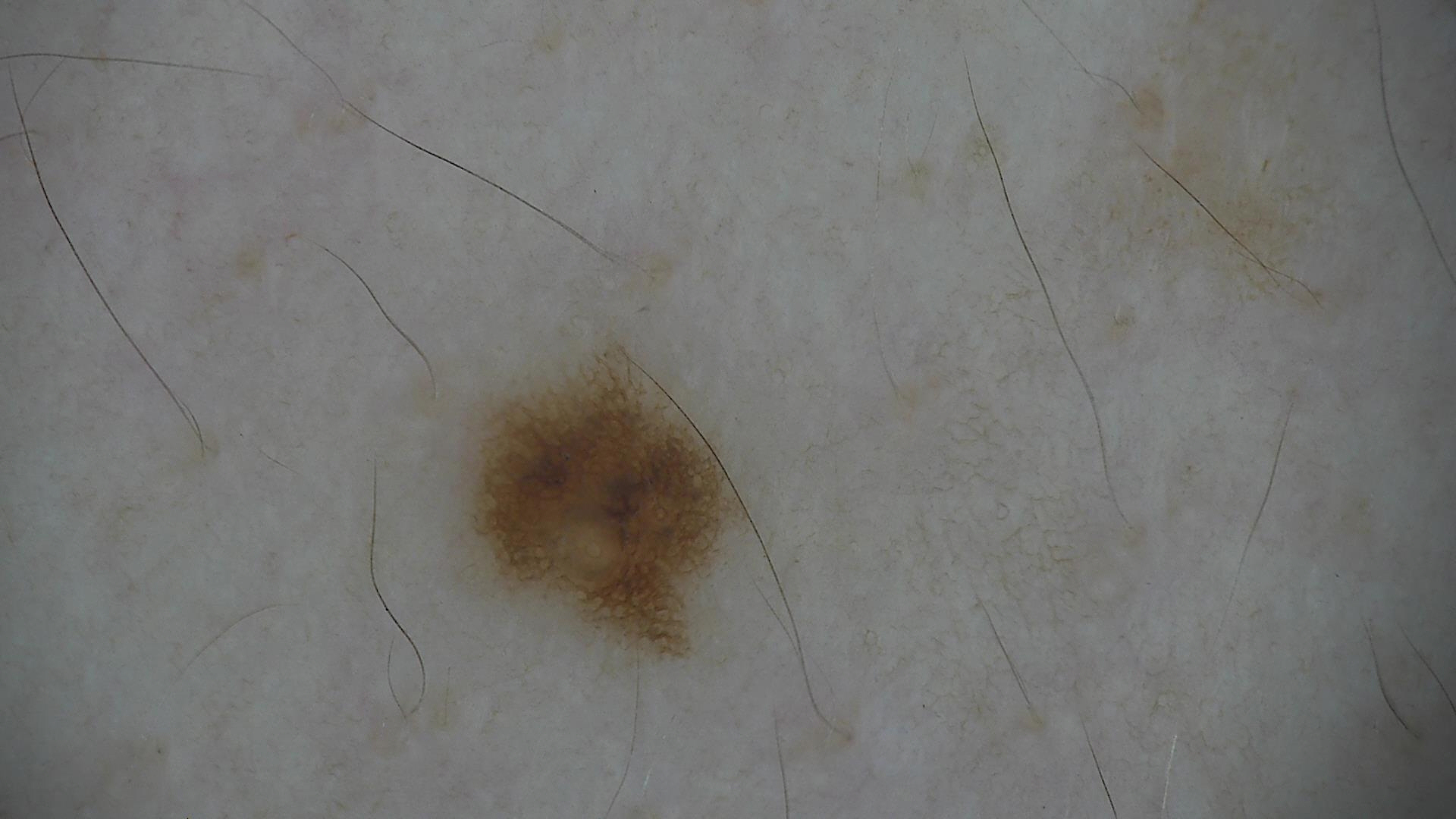{"diagnosis": {"name": "dysplastic junctional nevus", "code": "jd", "malignancy": "benign", "super_class": "melanocytic", "confirmation": "expert consensus"}}